The leg is involved · the photo was captured at a distance · the patient is 40–49, male: 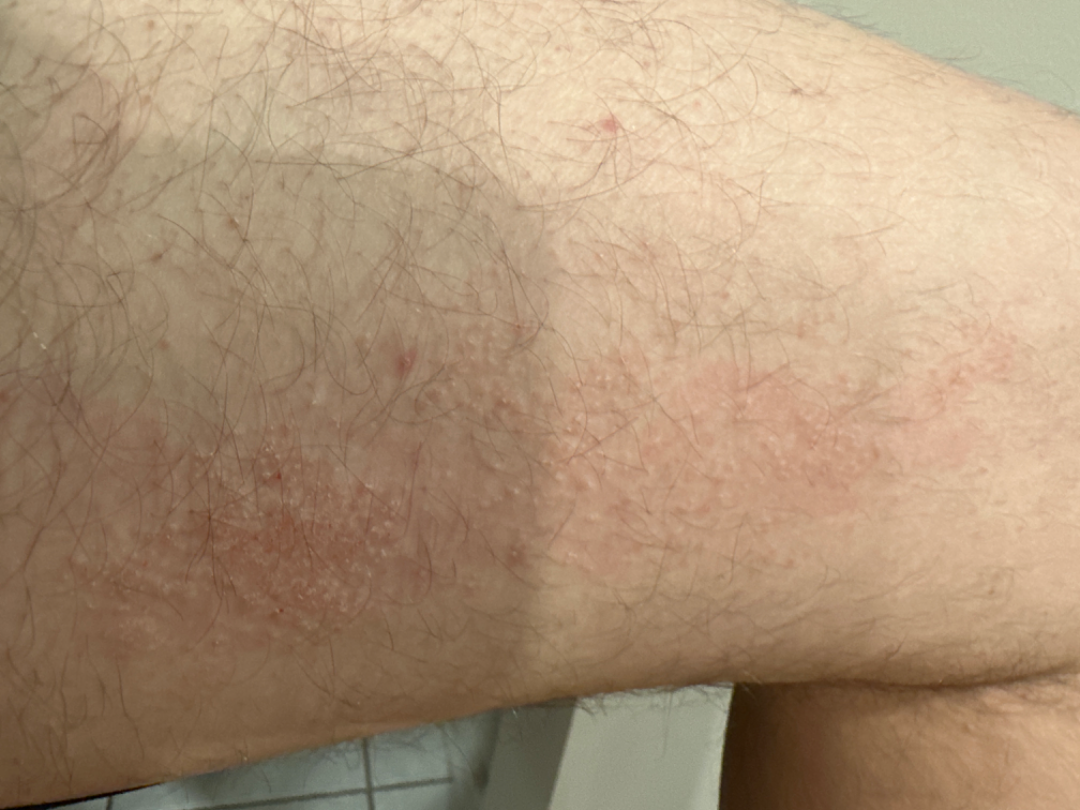clinical impression: the favored diagnosis is Eczema; also on the differential is Acute and chronic dermatitis; less probable is Tinea